A dermoscopic view of a skin lesion.
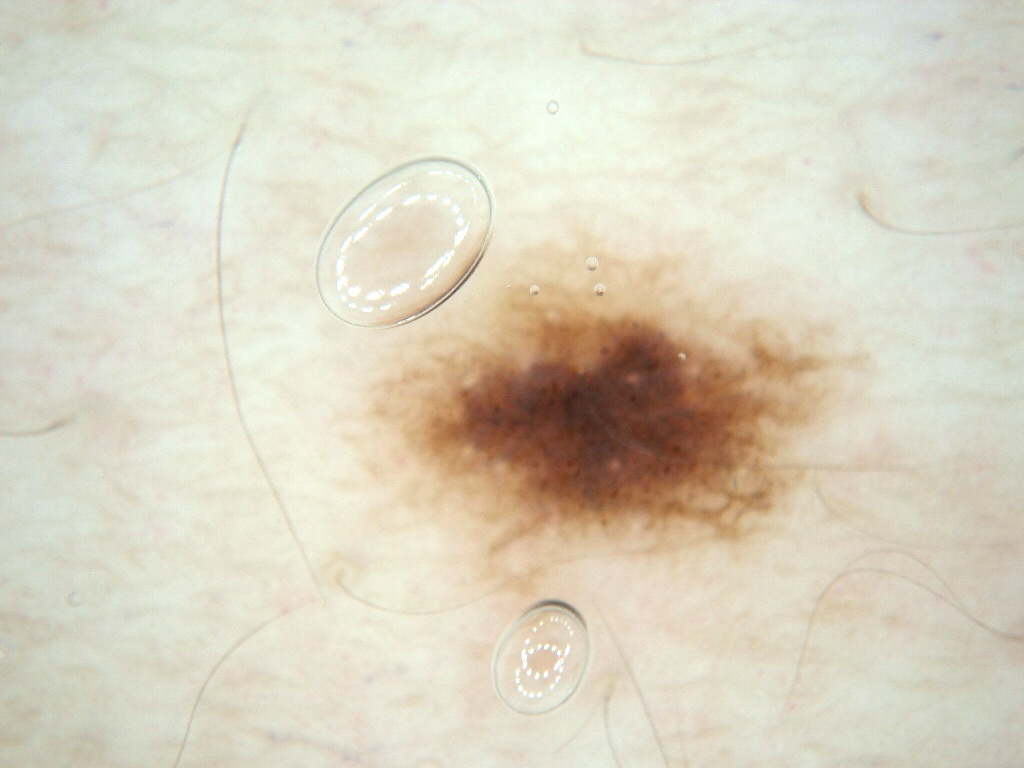| key | value |
|---|---|
| dermoscopic features assessed but absent | globules and streaks |
| lesion location | bbox=[374, 268, 829, 595] |
| lesion extent | ~12% of the field |
| impression | a benign skin lesion |